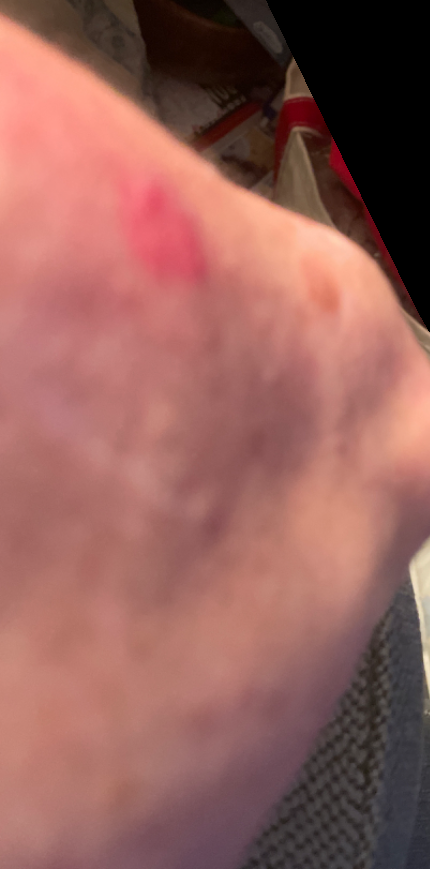Assessment: The reviewing dermatologist was unable to assign a differential diagnosis from the image. Clinical context: This is a close-up image. Texture is reported as raised or bumpy. The lesion is associated with bothersome appearance and itching. No constitutional symptoms were reported. The affected area is the arm. Self-categorized by the patient as a rash. The condition has been present for about one day.